This is a close-up image; reported lesion symptoms include bothersome appearance and itching; the patient indicates the lesion is fluid-filled and raised or bumpy; the contributor is 18–29, female; the patient considered this a rash; the affected area is the arm and leg; the patient indicates the condition has been present for one to four weeks; no associated systemic symptoms reported: 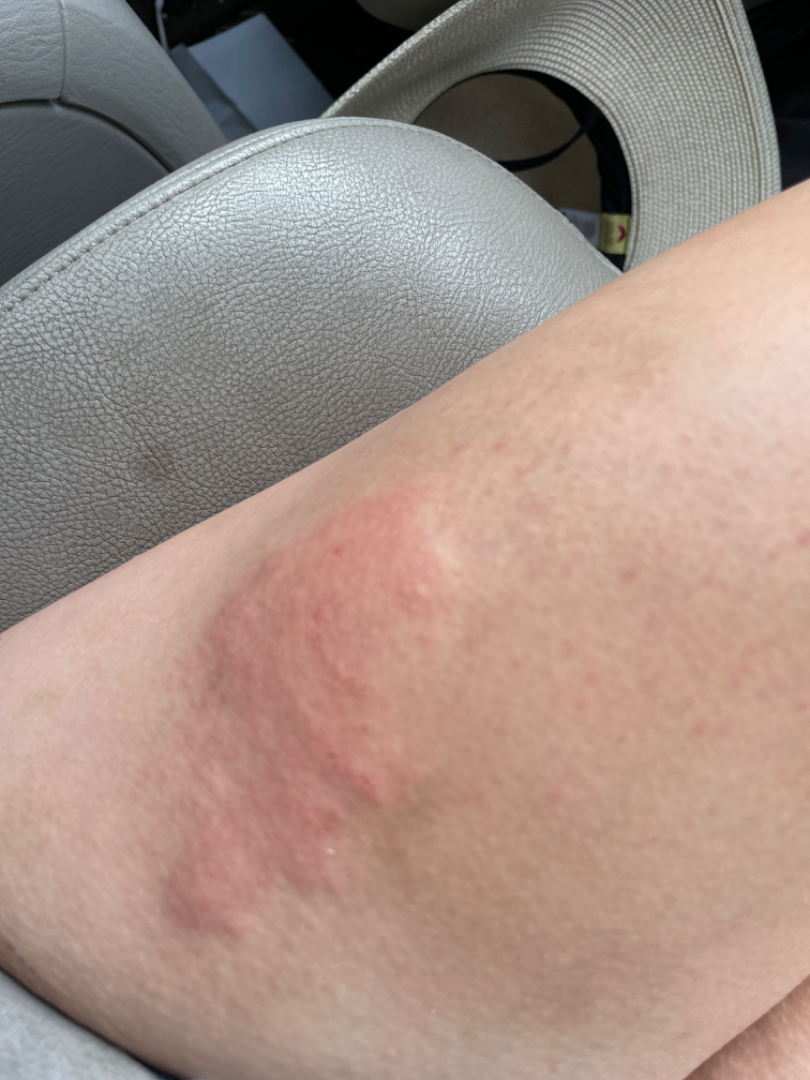Q: Could the case be diagnosed?
A: unable to determine